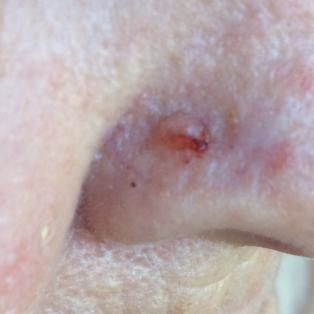Findings:
A smartphone photograph of a skin lesion. A female patient 64 years of age. The lesion involves the nose.
Conclusion:
Histopathological examination showed a basal cell carcinoma.